A patient 36 years of age — 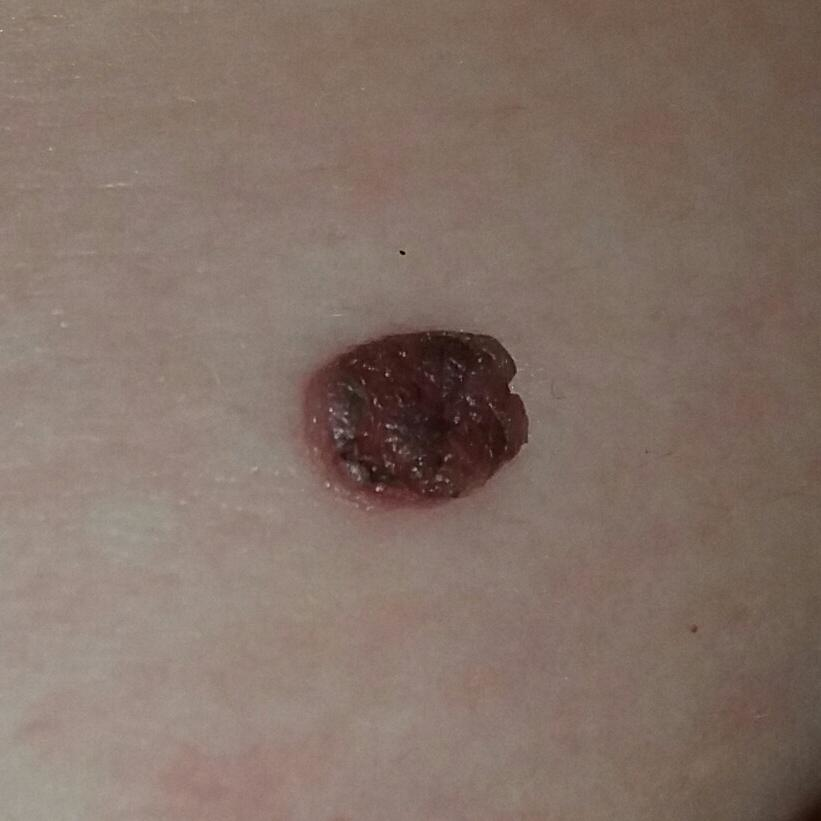Clinical context:
Located on the chest. Per patient report, the lesion is elevated and has grown.
Conclusion:
Expert review favored a nevus.